A female patient roughly 30 years of age; contact-polarized dermoscopy of a skin lesion:
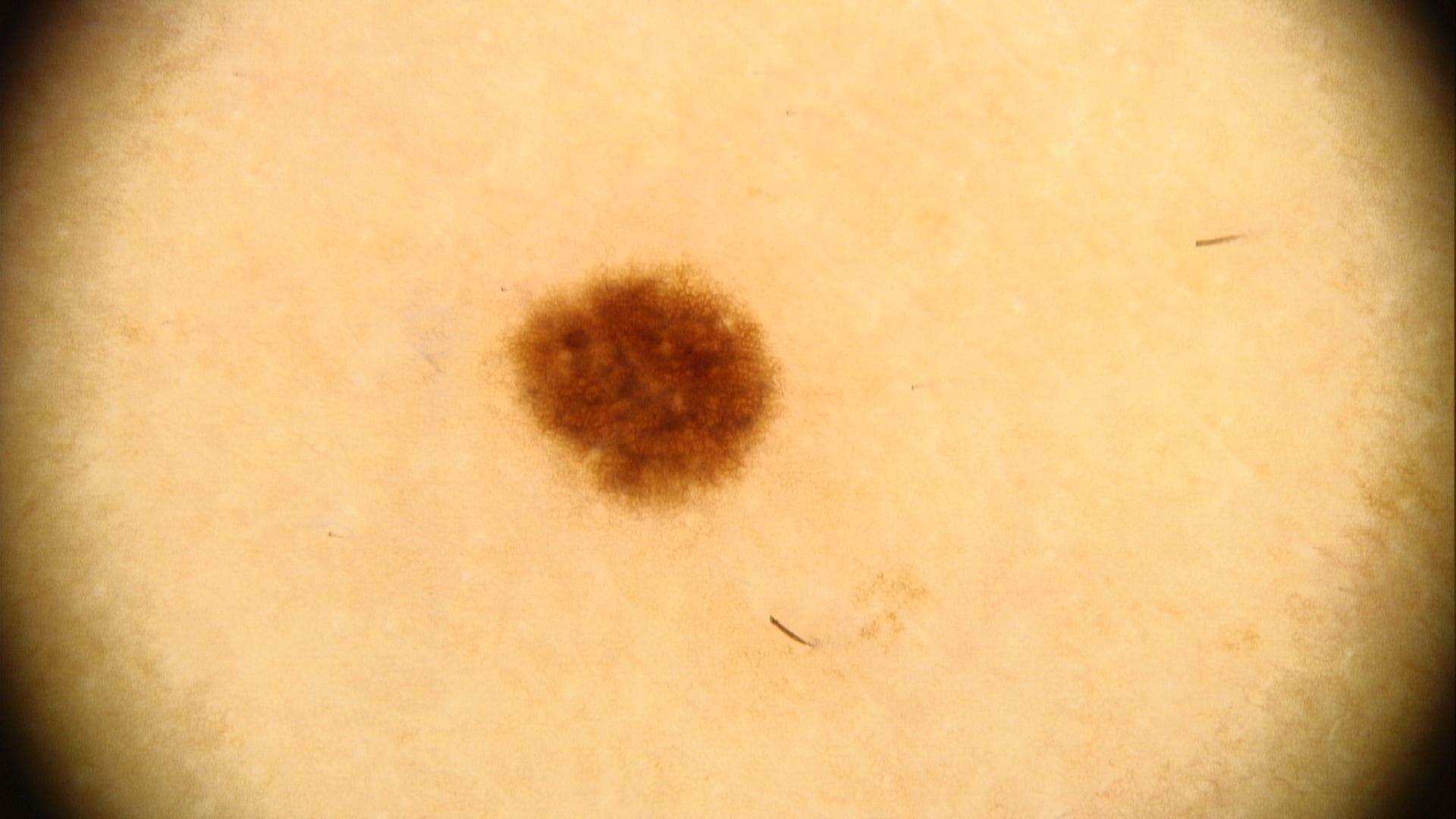The lesion was found on the trunk.
Clinically diagnosed as a benign lesion — a nevus.